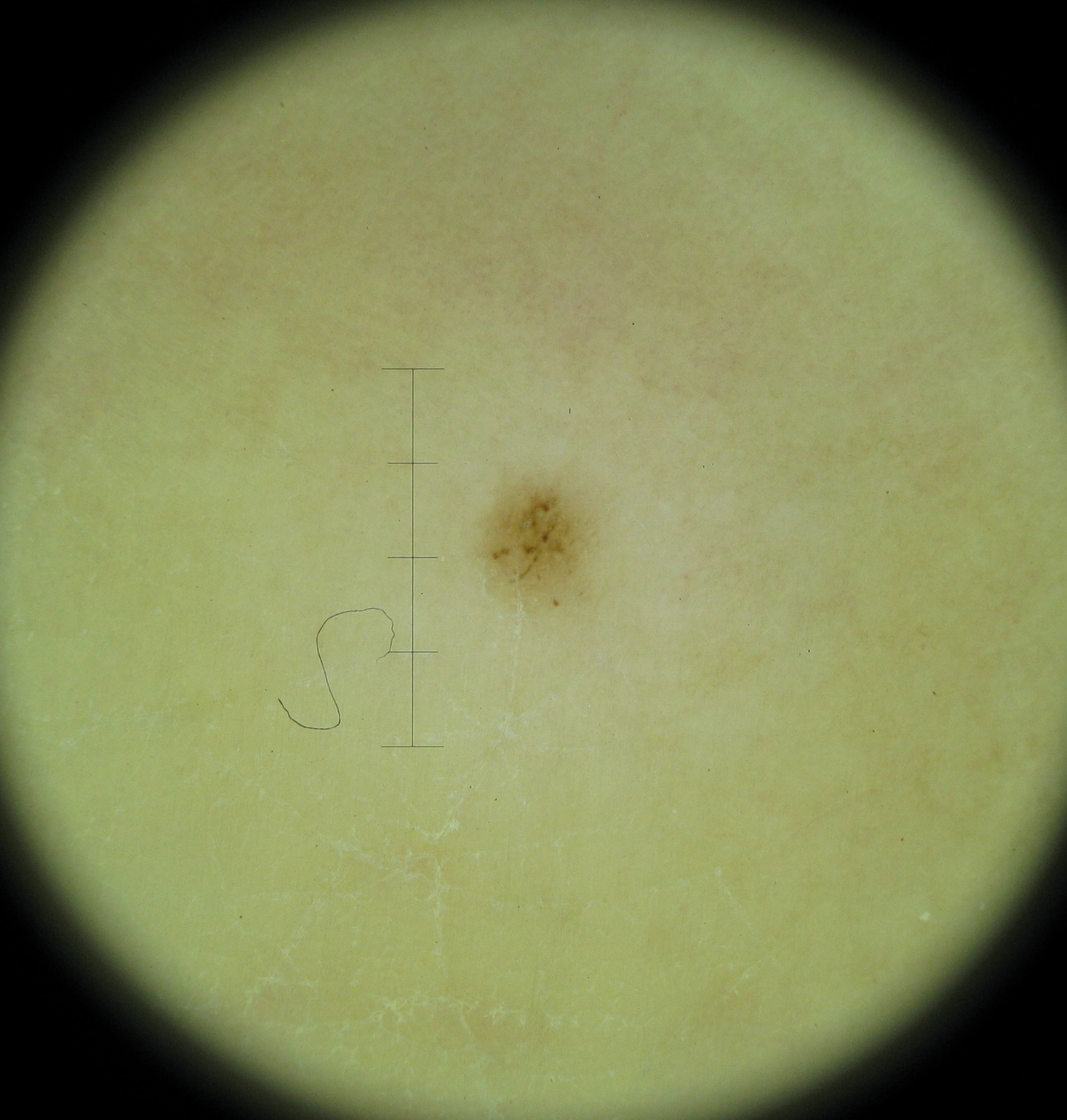Labeled as an acral dysplastic junctional nevus.